The patient says their skin tans without first burning; a male patient 72 years old; collected as part of a research study, without a referral diagnosis; a skin lesion imaged with a dermatoscope:
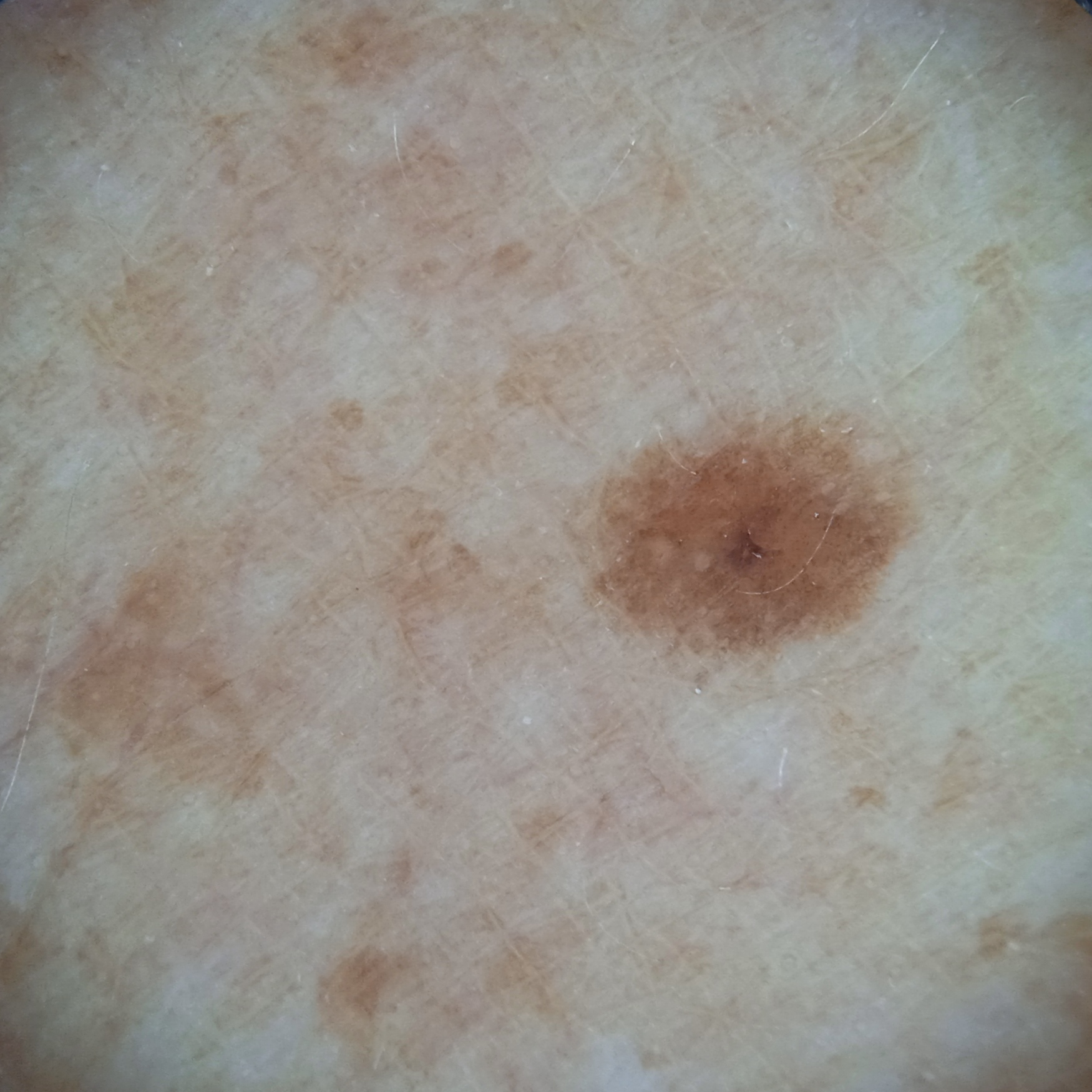The lesion is on the back. Measuring roughly 3.7 mm. The lesion was assessed as a melanocytic nevus.